A close-up photograph, the affected area is the leg:
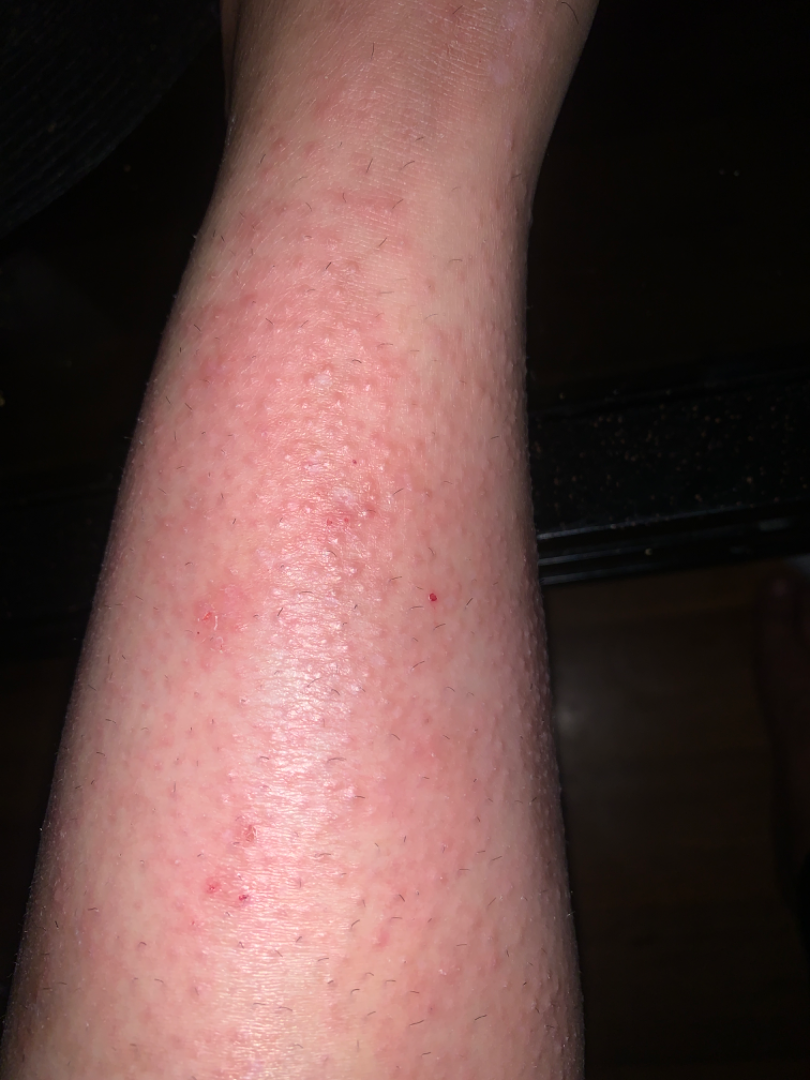Review: On photographic review by a dermatologist: Eczema (67%); Allergic Contact Dermatitis (33%).